A close-up photograph — 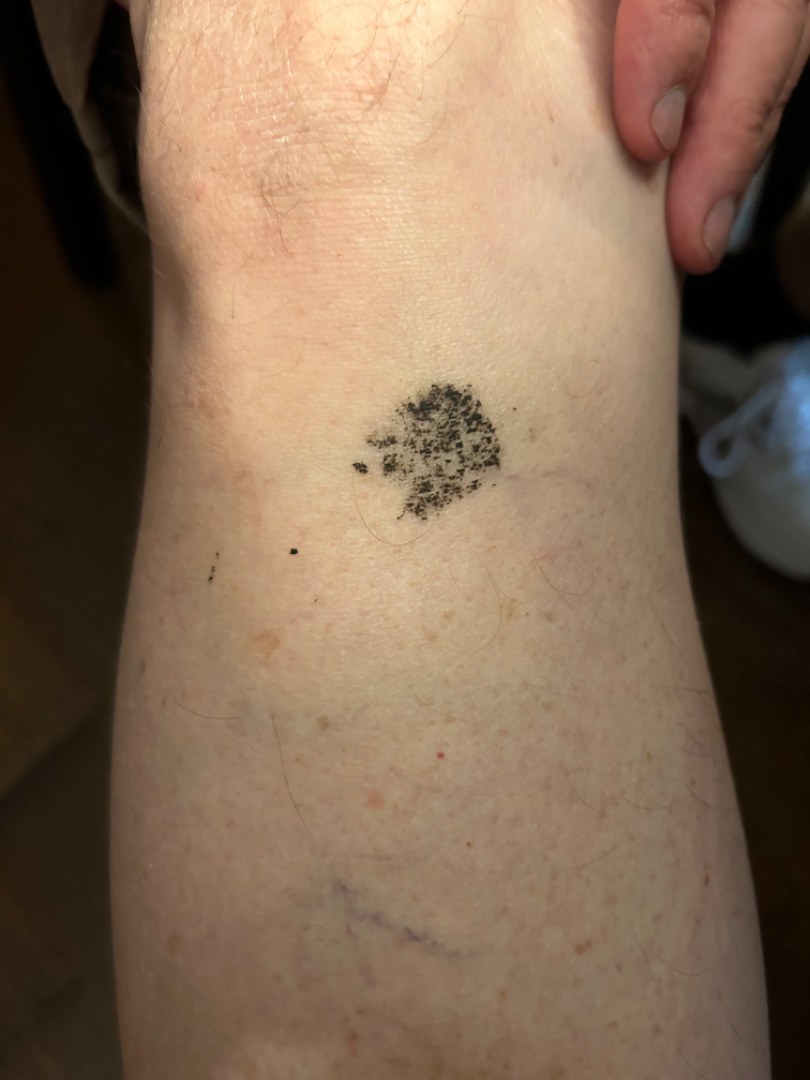Case summary:
- assessment — indeterminate